Female contributor, age 40–49 · close-up view · the lesion involves the leg — 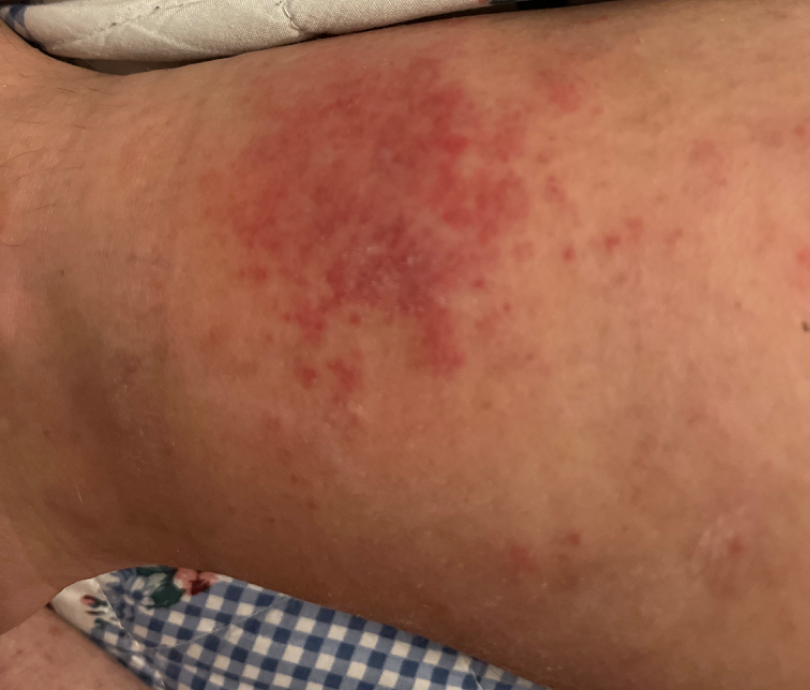history: about one day
reported symptoms: none reported
other reported symptoms: none reported
lesion texture: raised or bumpy
patient describes the issue as: a rash
differential diagnosis: consistent with Stasis Dermatitis